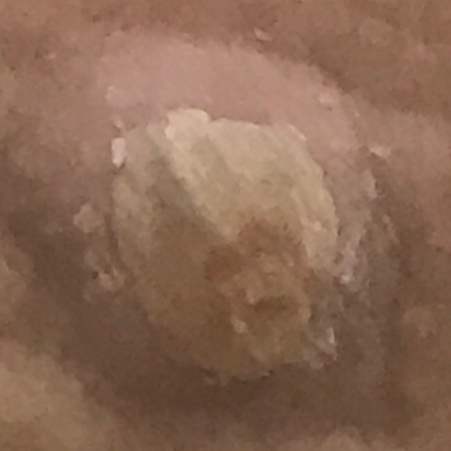exposure history: prior skin cancer (patient or family), prior malignancy (patient or family) | skin type: II | patient: female, in their 70s | modality: clinical photo | body site: a forearm | diameter: approx. 10 × 9 mm | reported symptoms: itching | diagnosis: actinic keratosis (biopsy-proven).